The lesion is described as raised or bumpy and fluid-filled; the contributor is 18–29, male; the photograph is a close-up of the affected area; the arm is involved; reported duration is less than one week; the patient described the issue as a rash — 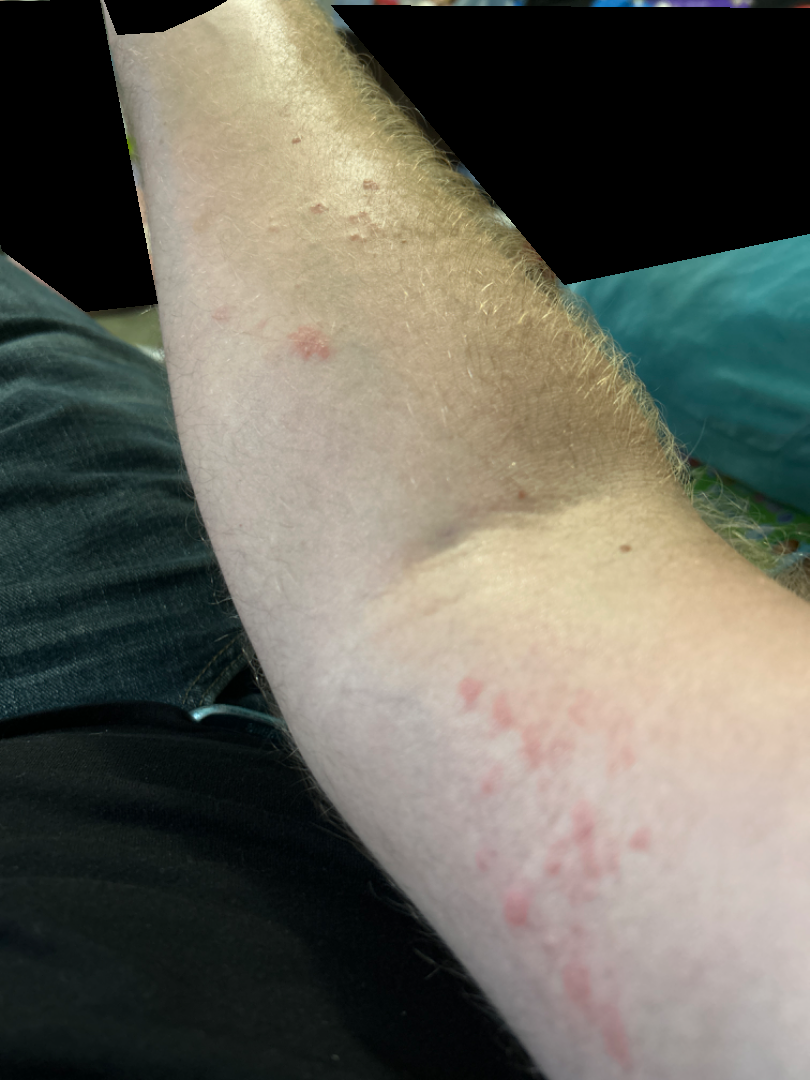| field | value |
|---|---|
| assessment | indeterminate from the photograph |